This is a close-up image.
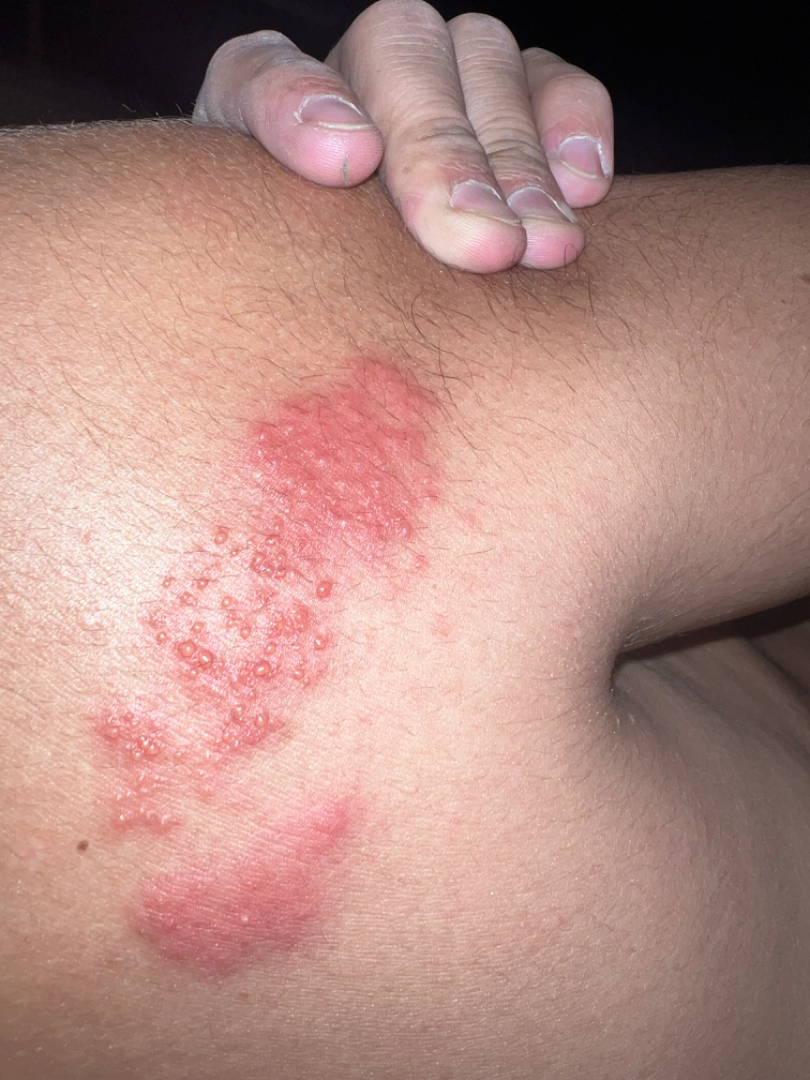differential diagnosis=the leading consideration is Herpes Zoster; also consider Allergic Contact Dermatitis